A subject in their mid-50s; recorded as Fitzpatrick II; a dermatoscopic image of a skin lesion.
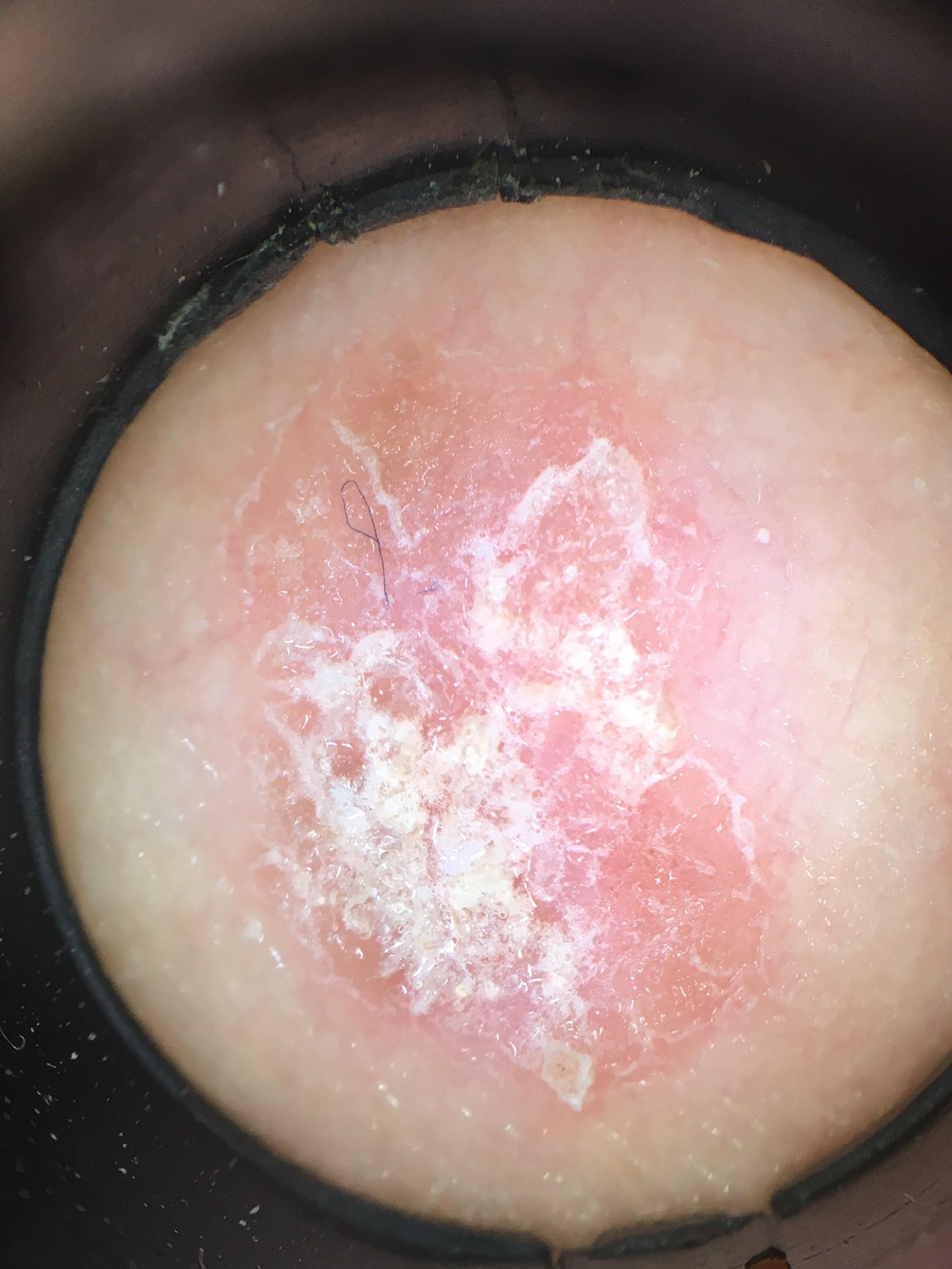site: a lower extremity; diagnosis: Squamous cell carcinoma (biopsy-proven).